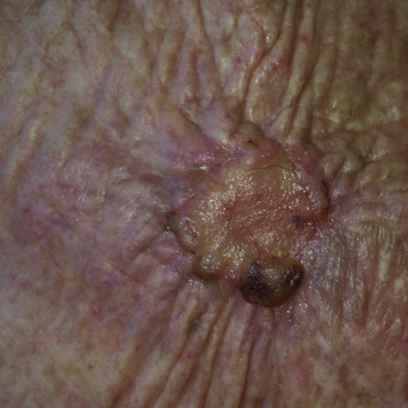<record>
<patient>
<age>78</age>
<gender>female</gender>
</patient>
<image>clinical photo</image>
<risk_factors>
<positive>prior skin cancer (patient or family), prior cancer (patient or family)</positive>
</risk_factors>
<lesion_size>
<diameter_1_mm>20.0</diameter_1_mm>
<diameter_2_mm>18.0</diameter_2_mm>
</lesion_size>
<symptoms>
<present>change in appearance, pain, elevation, growth, bleeding, itching</present>
</symptoms>
<diagnosis>
<name>basal cell carcinoma</name>
<code>BCC</code>
<malignancy>malignant</malignancy>
<confirmation>histopathology</confirmation>
</diagnosis>
</record>